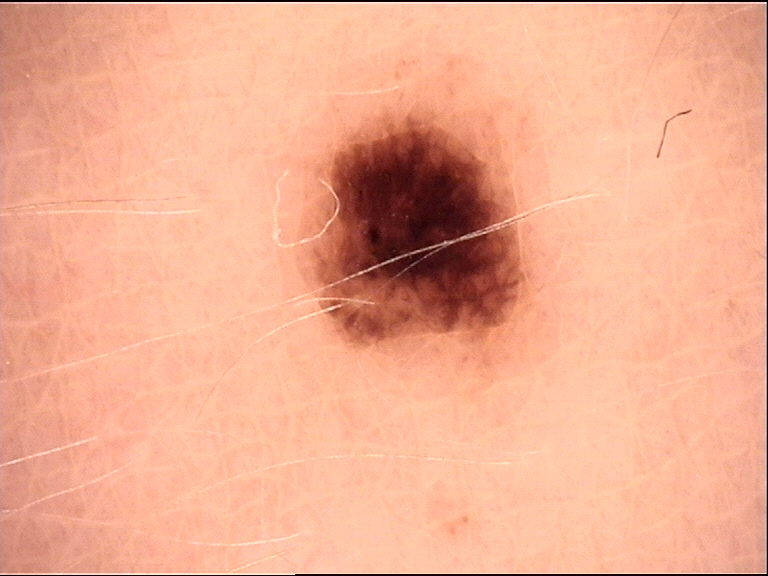{
  "image": "dermoscopy",
  "diagnosis": {
    "name": "dysplastic junctional nevus",
    "code": "jd",
    "malignancy": "benign",
    "super_class": "melanocytic",
    "confirmation": "expert consensus"
  }
}